A dermoscopy image of a single skin lesion · a female subject, aged approximately 45.
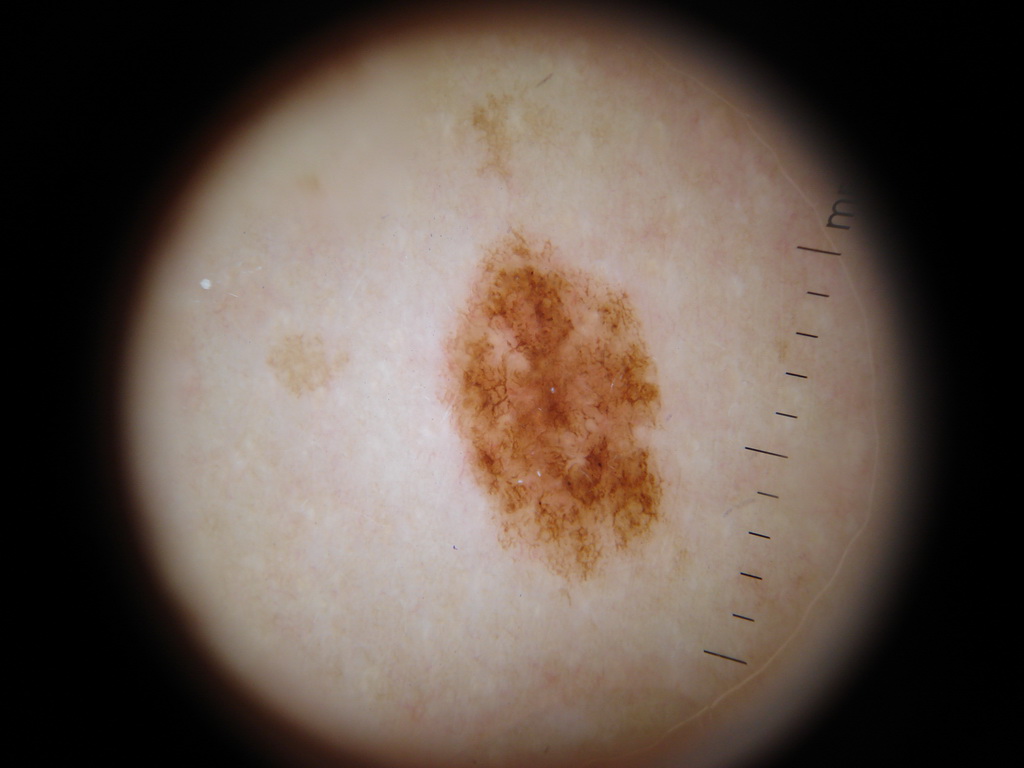Dermoscopic assessment notes pigment network. In (x1, y1, x2, y2) order, the lesion is located at 434, 221, 680, 612. Clinically diagnosed as a melanocytic nevus.